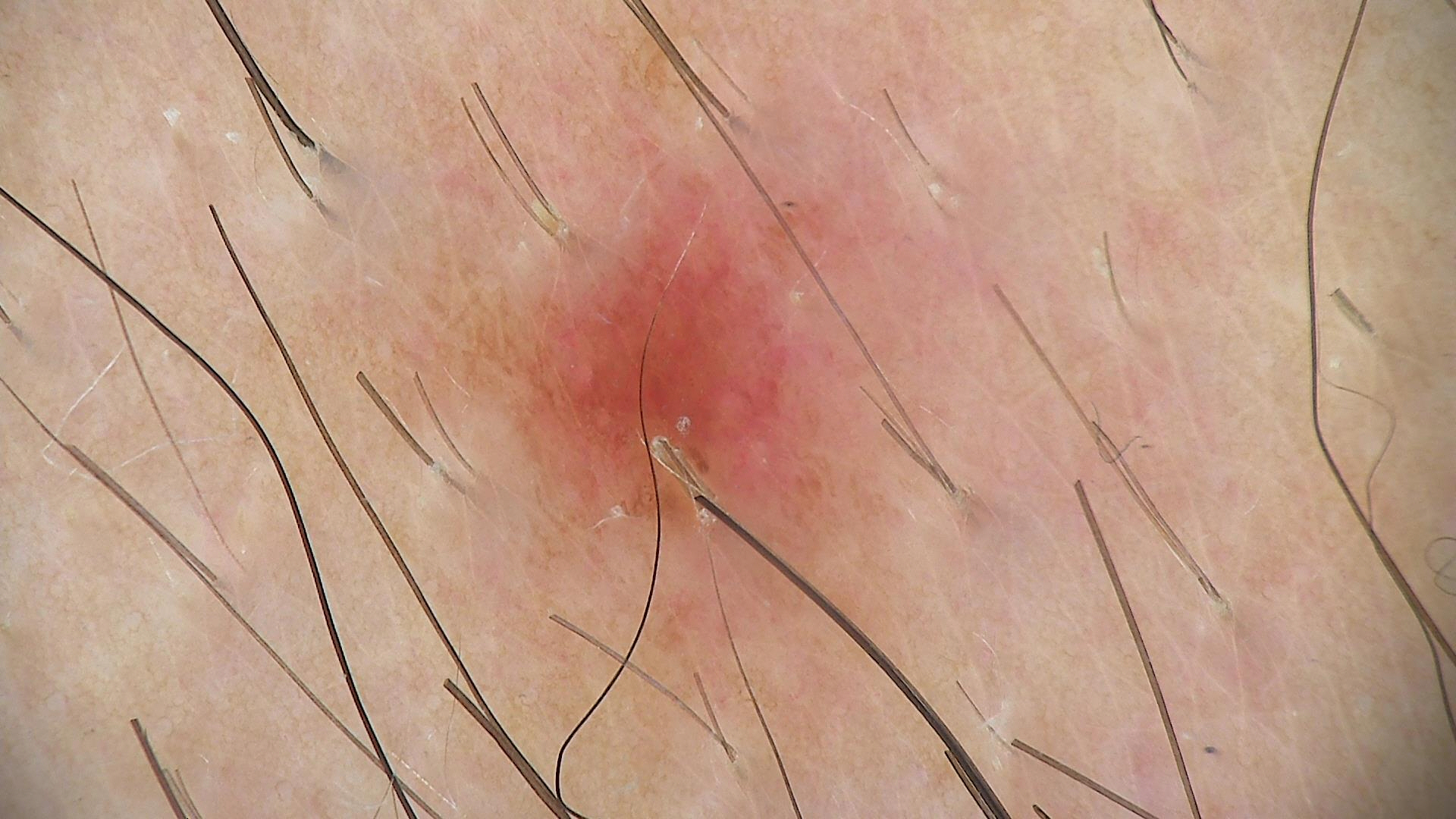Diagnosed as a benign lesion — a dysplastic junctional nevus.